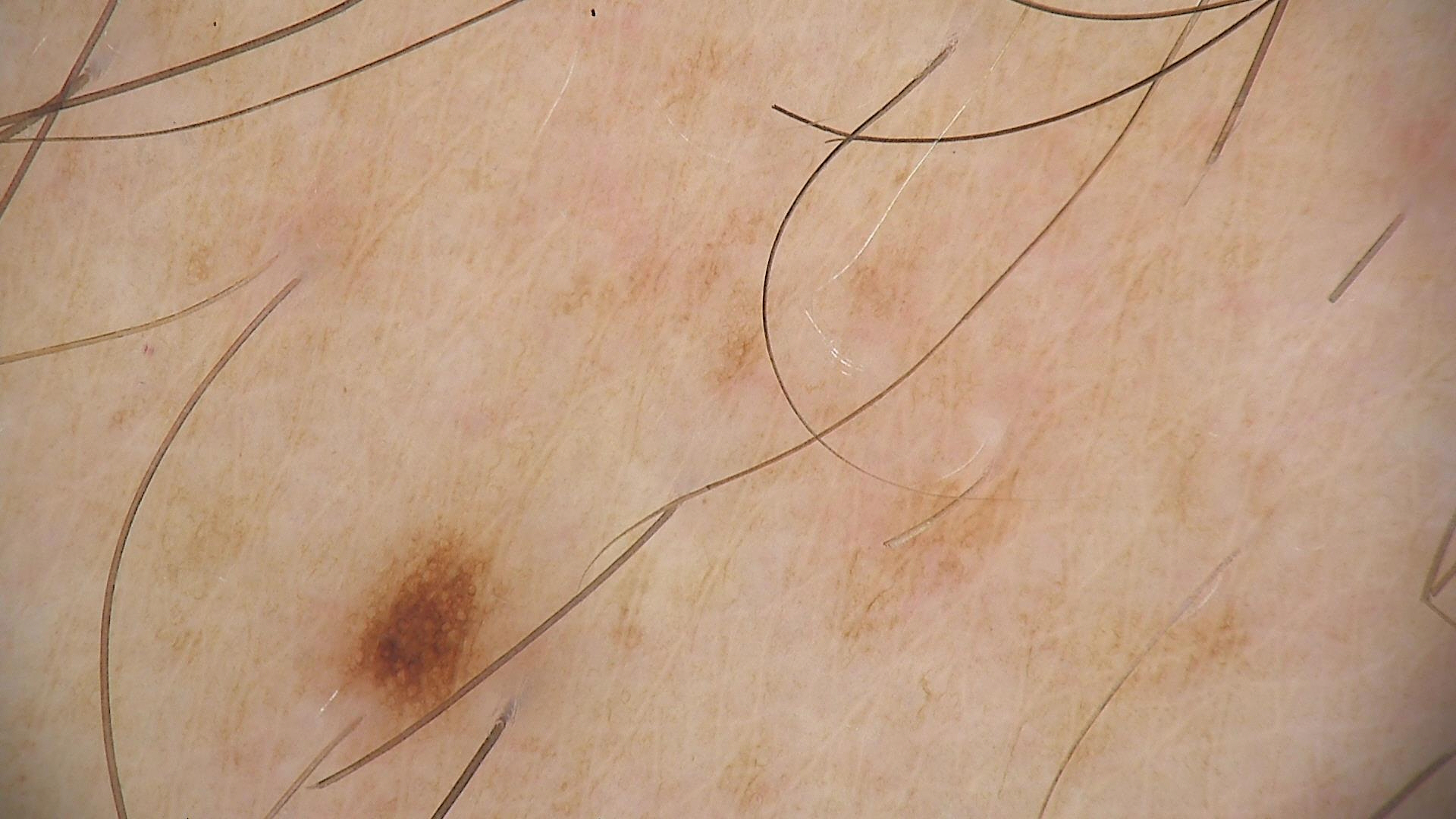assessment=dysplastic junctional nevus (expert consensus).